A female patient aged 53-57, this is a dermoscopic photograph of a skin lesion:
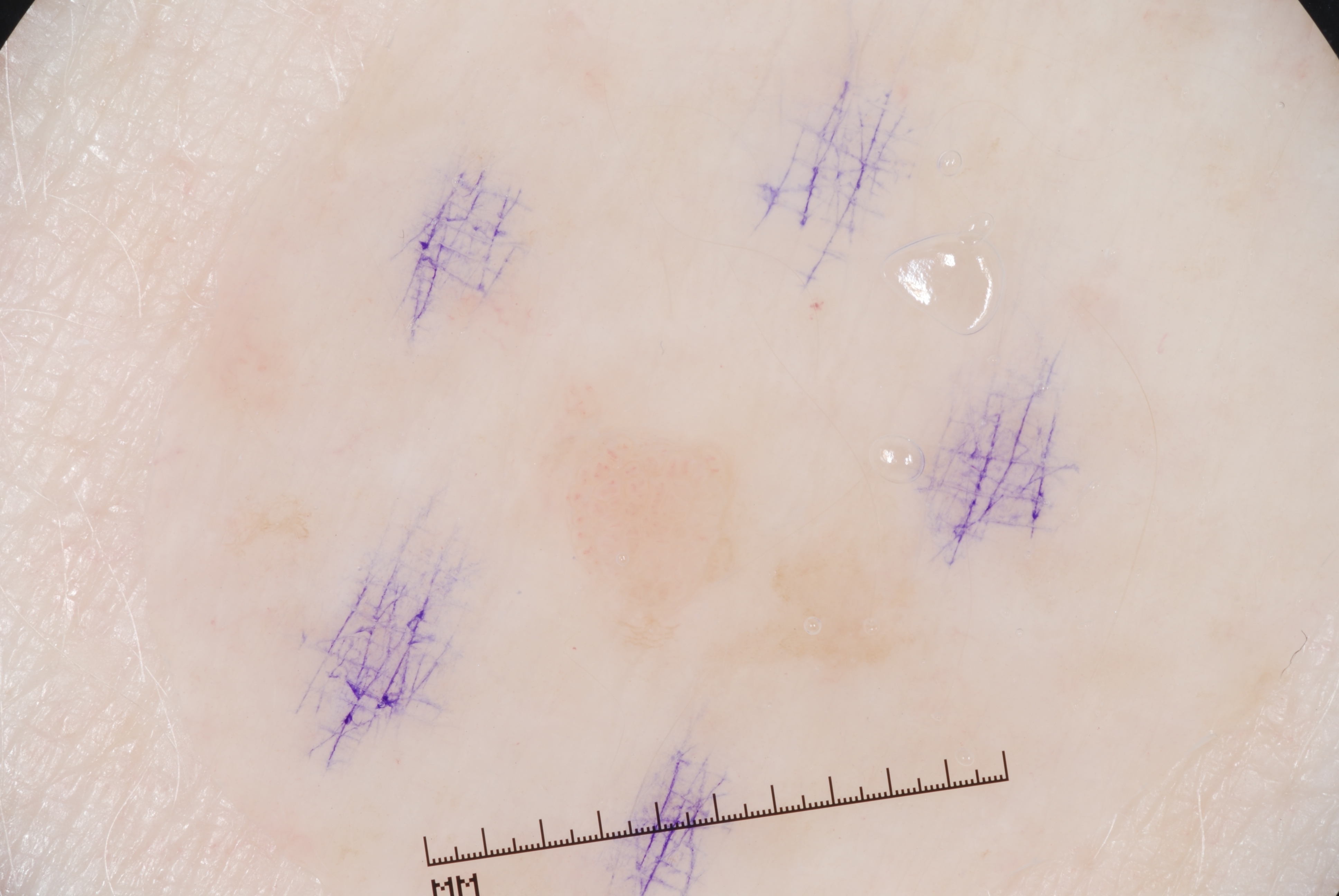Image and clinical context:
As (left, top, right, bottom), the visible lesion spans (540, 385, 756, 654). The lesion covers approximately 2% of the dermoscopic field. Dermoscopic review identifies pigment network, with no milia-like cysts, streaks, or negative network.
Conclusion:
The clinical diagnosis was a seborrheic keratosis, a keratinocytic lesion.